The leg, back of the hand, palm, arm and top or side of the foot are involved. Close-up view:
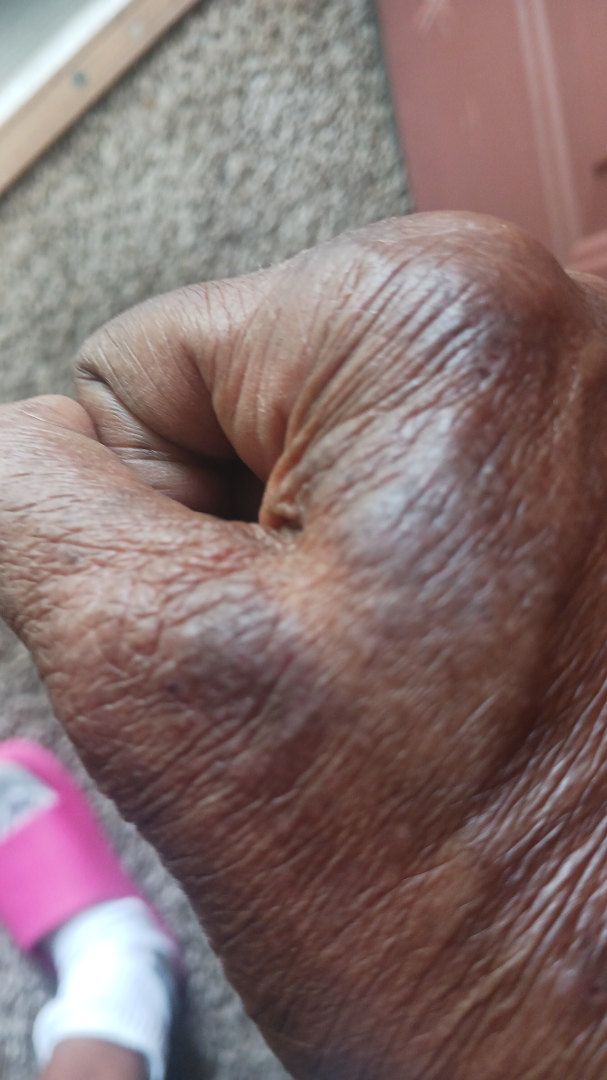The dermatologist could not determine a likely condition from the photograph alone.